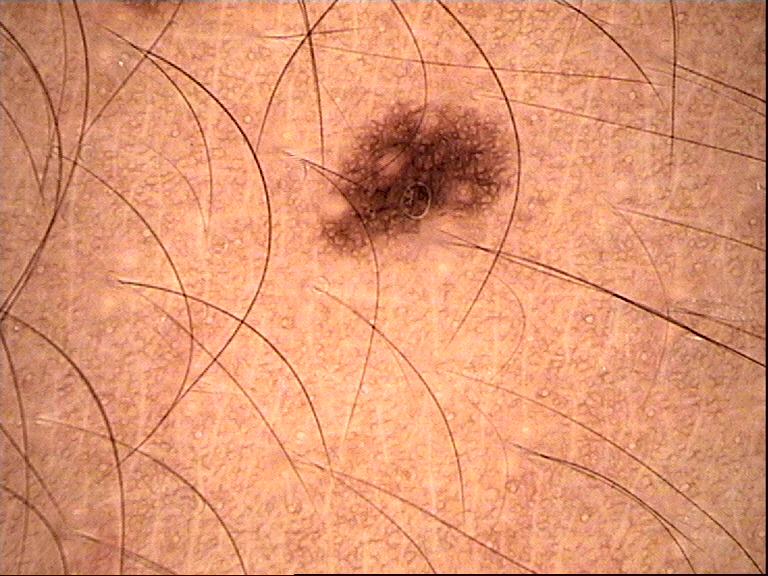Dermoscopy of a skin lesion.
Labeled as a dysplastic junctional nevus.